A dermatoscopic image of a skin lesion.
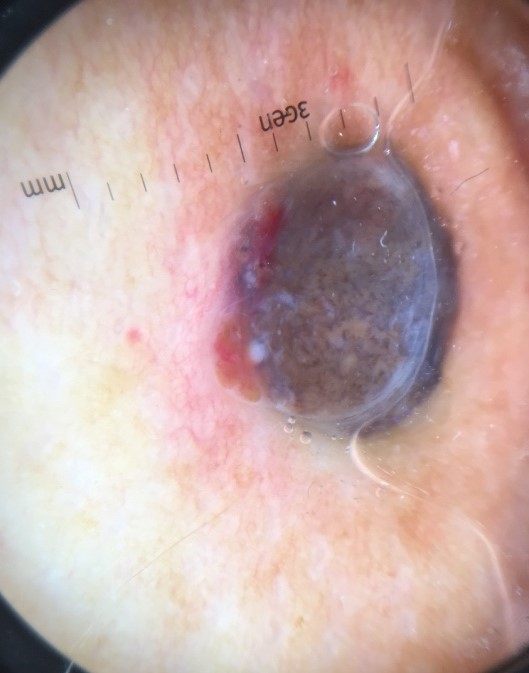Biopsy-confirmed as a melanoma.